The patient also reports fatigue, fever and joint pain; the patient notes the condition has been present for one to four weeks; this is a close-up image; the patient notes the lesion is raised or bumpy; self-categorized by the patient as a rash; located on the leg; the patient notes enlargement and itching:
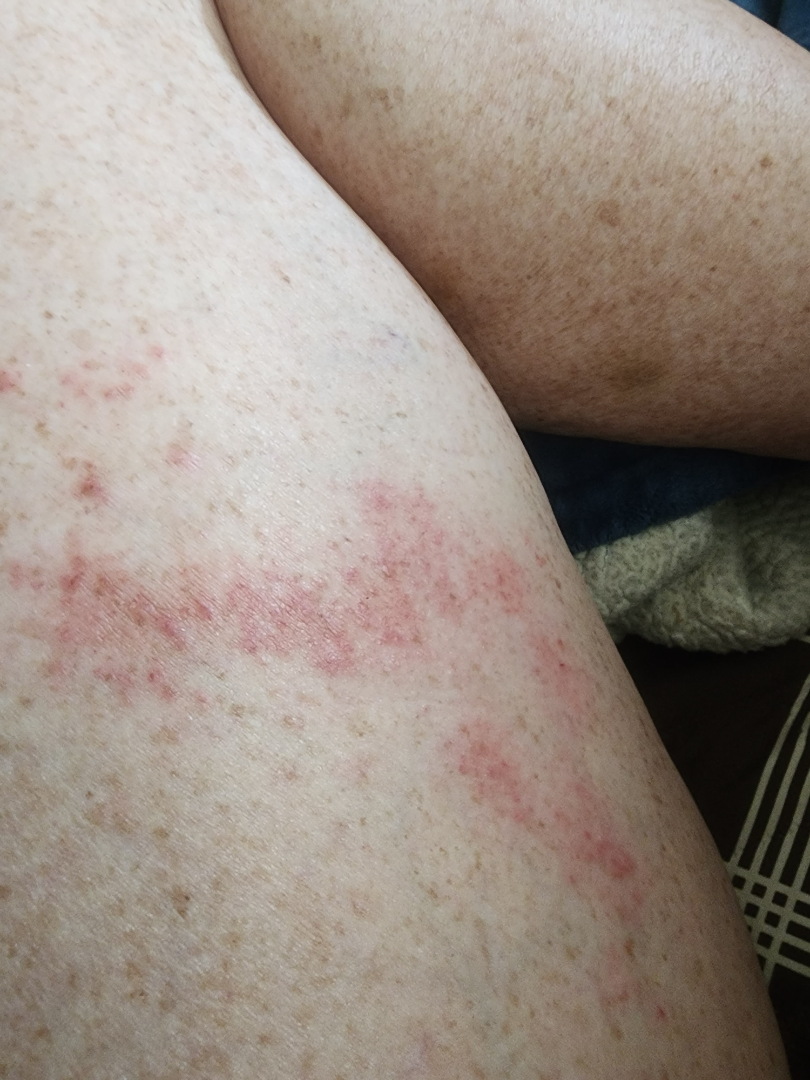{
  "assessment": "unable to determine"
}